A dermoscopic image of a skin lesion:
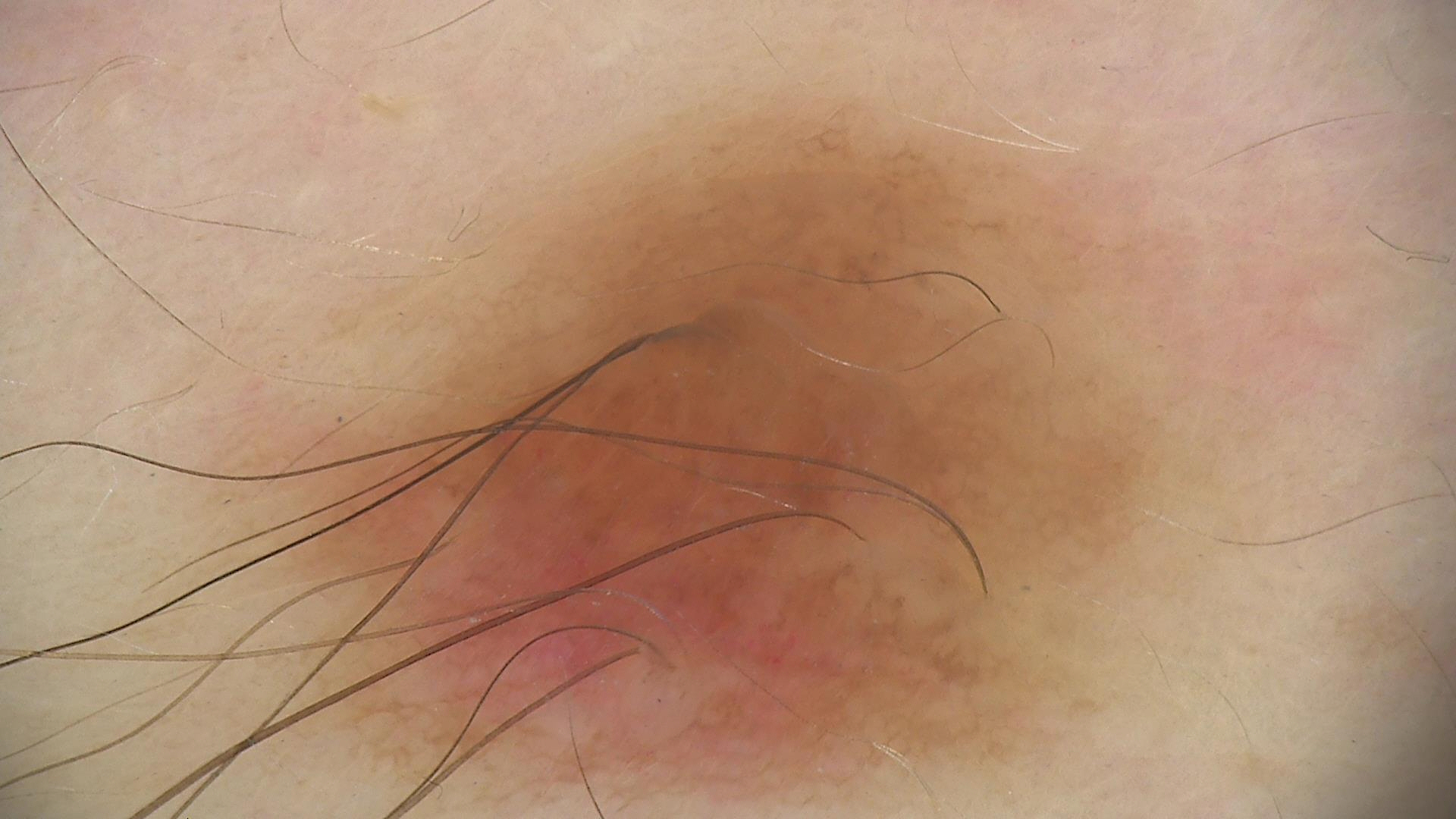Diagnosed as a compound nevus.